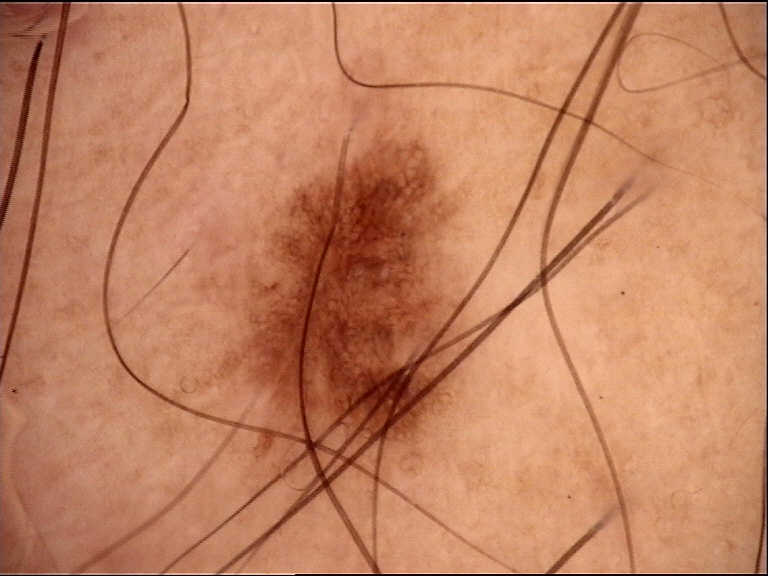{
  "diagnosis": {
    "name": "dysplastic junctional nevus",
    "code": "jd",
    "malignancy": "benign",
    "super_class": "melanocytic",
    "confirmation": "expert consensus"
  }
}